The patient considered this a rash. An image taken at an angle. Fitzpatrick phototype III; lay graders estimated Monk Skin Tone 4 (US pool) or 3 (India pool). No relevant systemic symptoms. Reported duration is one to four weeks. Symptoms reported: itching. The patient notes the lesion is raised or bumpy. The front of the torso is involved: 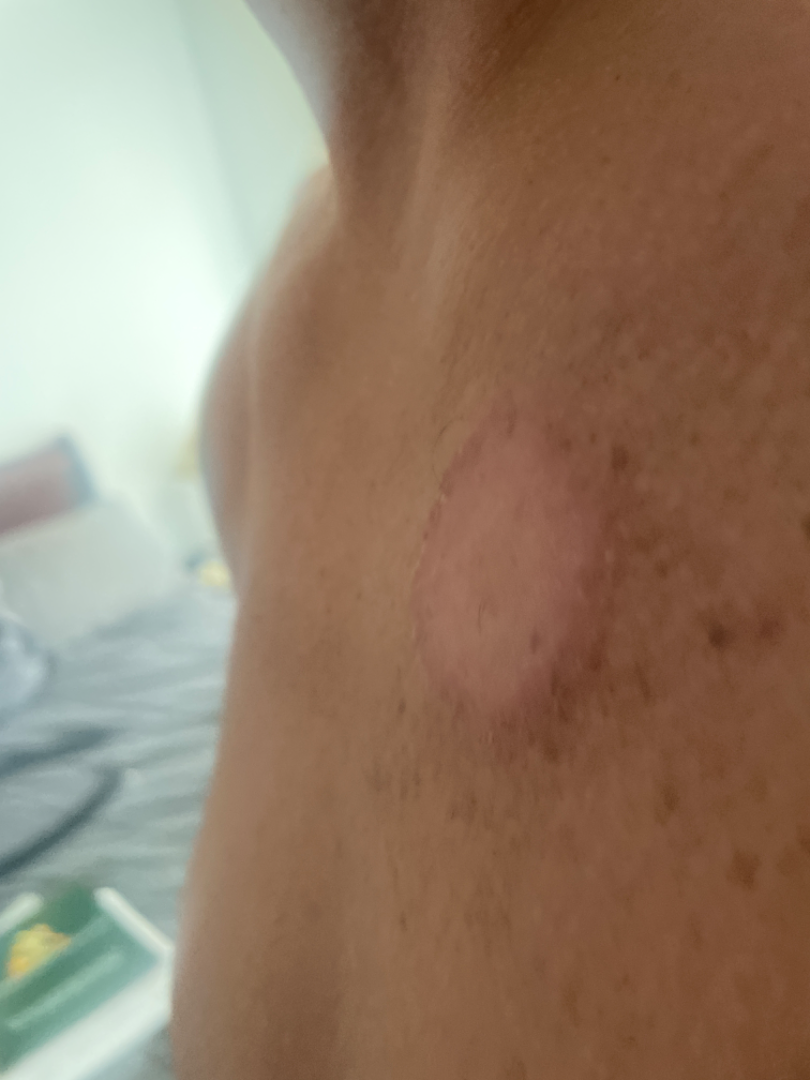The reviewing dermatologist's impression was: the favored diagnosis is Tinea; also raised was Inflicted skin lesions.